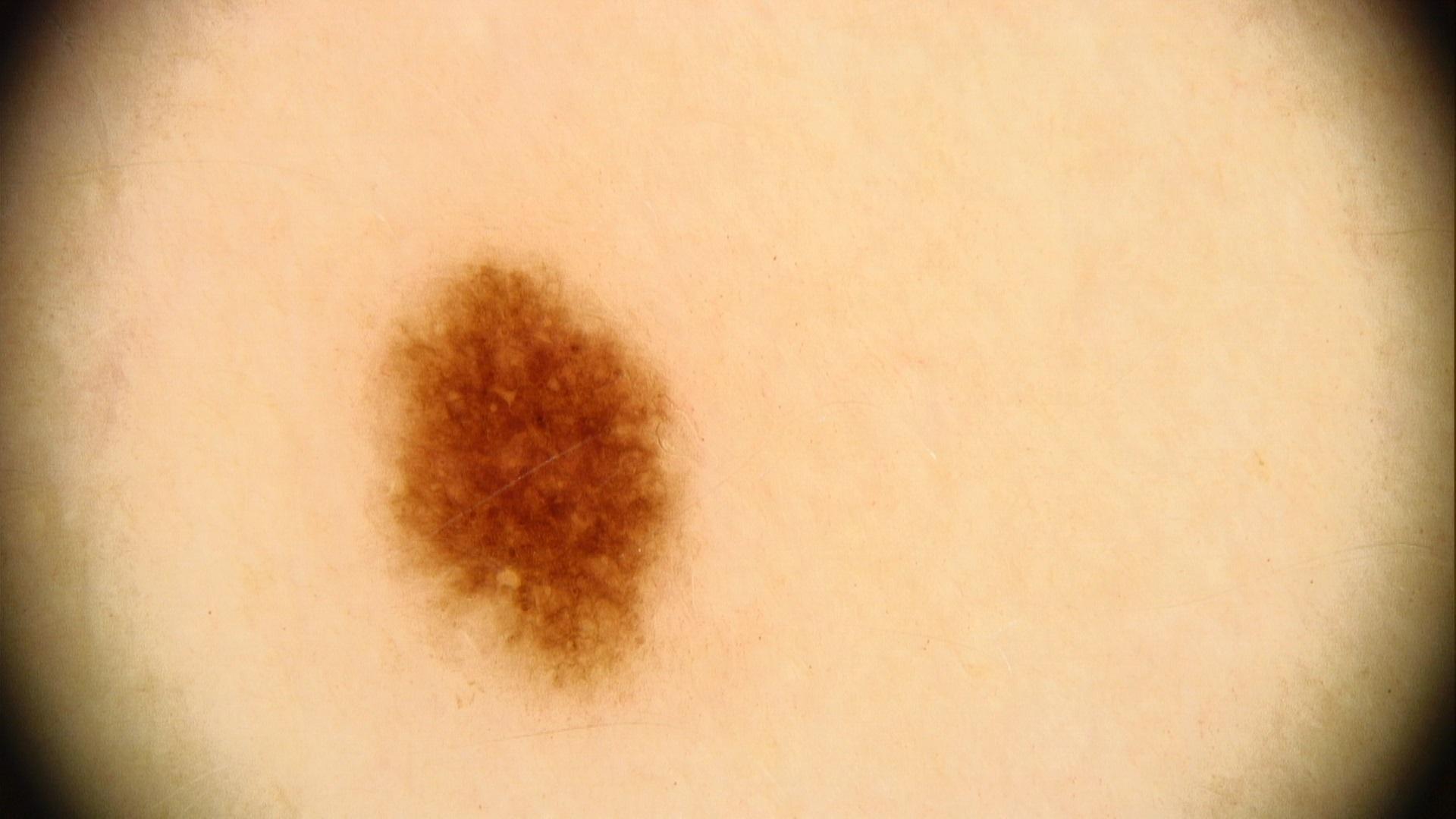image: contact-polarized dermoscopy | anatomic site: the trunk, specifically the anterior trunk | assessment: Nevus.